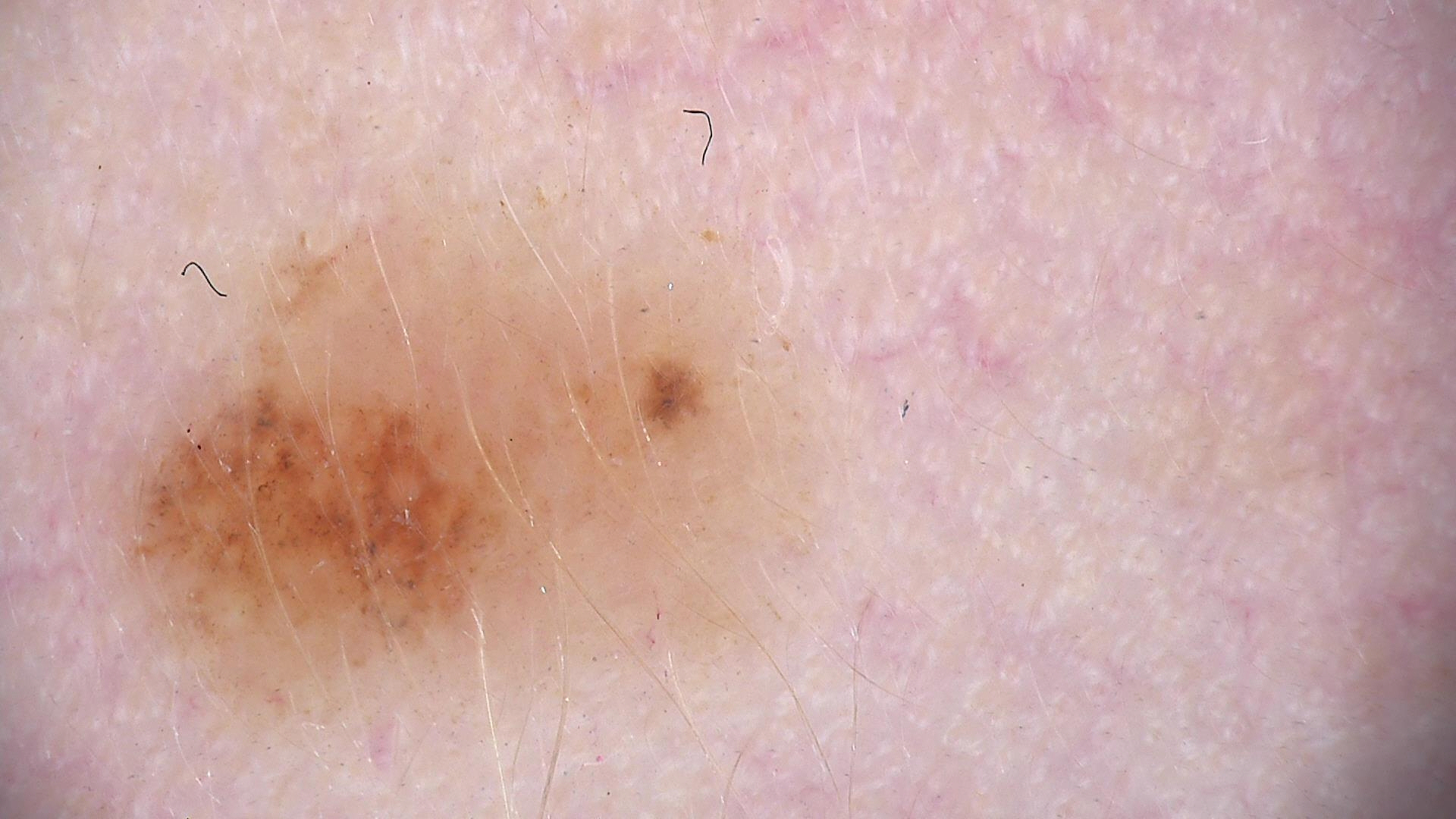Impression:
Classified as a benign lesion — a dysplastic compound nevus.